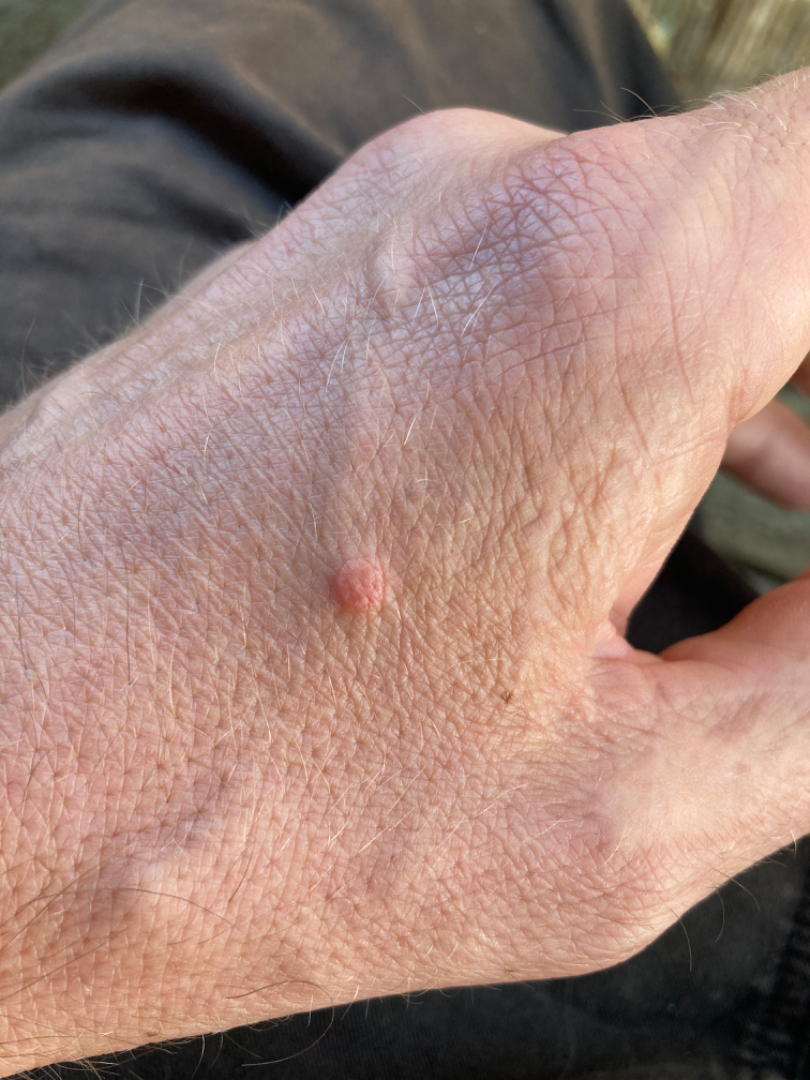This is a close-up image. On teledermatology review, Melanocytic Nevus, SK/ISK and Verruca vulgaris were considered with similar weight.